A dermoscopic image of a skin lesion.
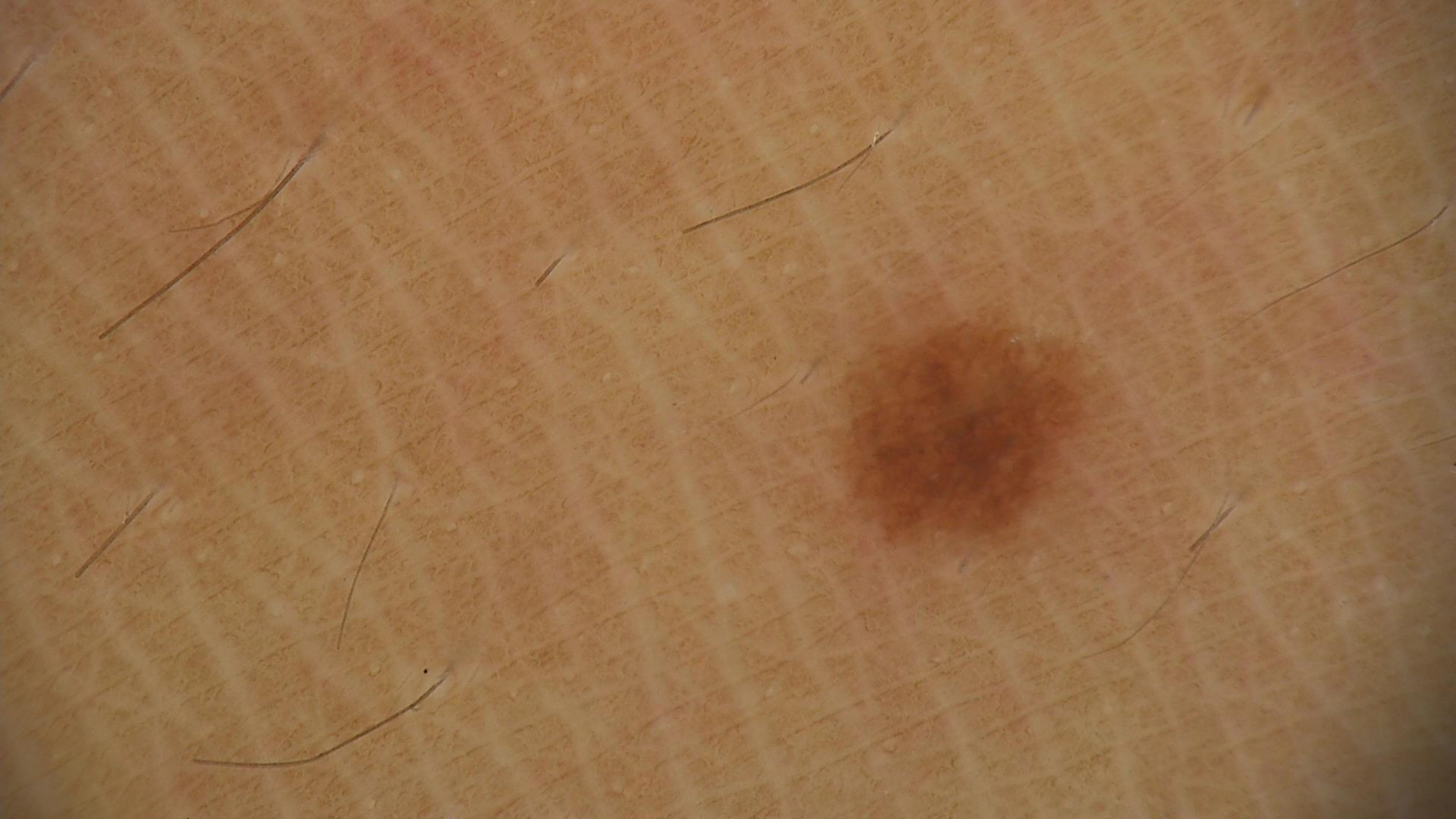Classified as a benign lesion — a dysplastic junctional nevus.